The patient is a female aged 18–29 · this image was taken at a distance · the lesion involves the leg.
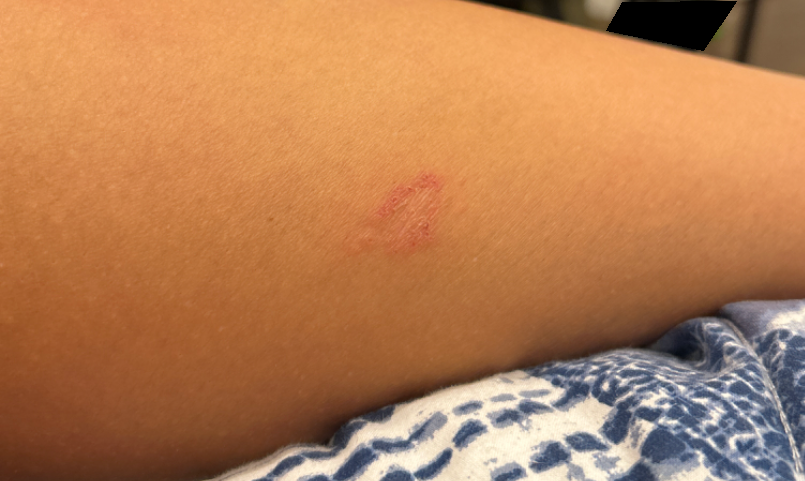History:
Reported lesion symptoms include itching. Texture is reported as raised or bumpy and rough or flaky. Fitzpatrick phototype III. The patient notes the condition has been present for one to four weeks.
Impression:
On photographic review by a dermatologist, most likely Superficial wound of body region; an alternative is Tinea; also consider Eczema.